An image taken at an angle. The arm and leg are involved. Male subject, age 40–49.
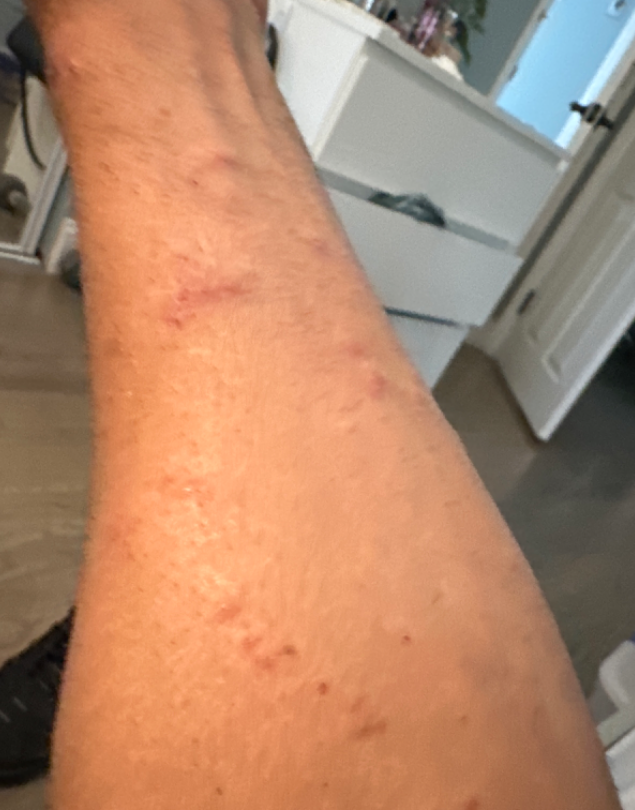assessment=Folliculitis (weight 0.57); Allergic Contact Dermatitis (weight 0.33); Localized skin infection (weight 0.10).